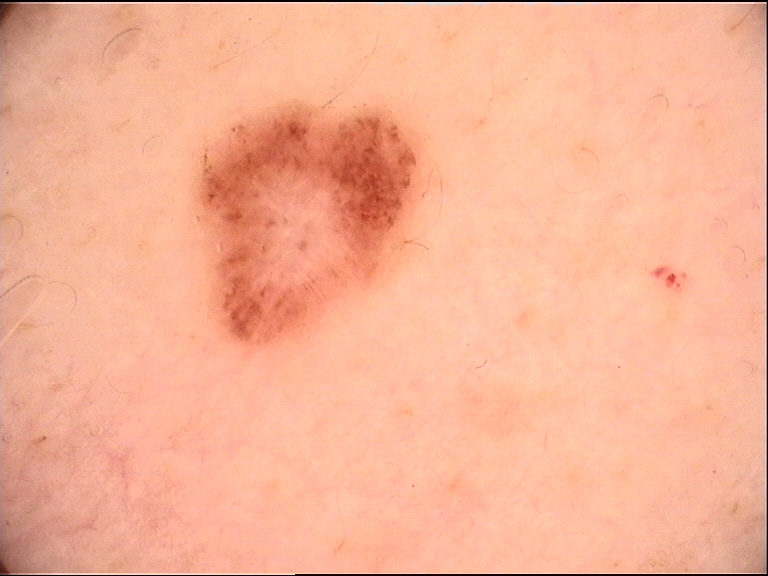Findings: A dermoscopic photograph of a skin lesion. Impression: Diagnosed as a dysplastic compound nevus.